The patient considered this a rash. The patient reports the condition has been present for one to three months. Located on the arm. This image was taken at a distance. Reported lesion symptoms include itching, pain and bleeding. The patient reports the lesion is raised or bumpy and fluid-filled. The contributor is male: 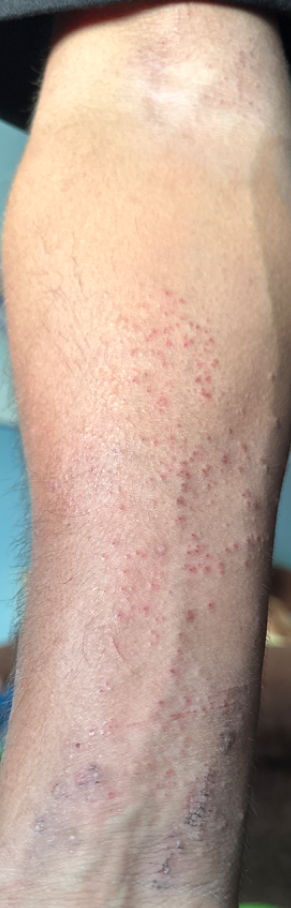Impression:
Eczema (weight 0.35); Acute dermatitis, NOS (weight 0.26); Allergic Contact Dermatitis (weight 0.26); Lichen planus/lichenoid eruption (weight 0.13).